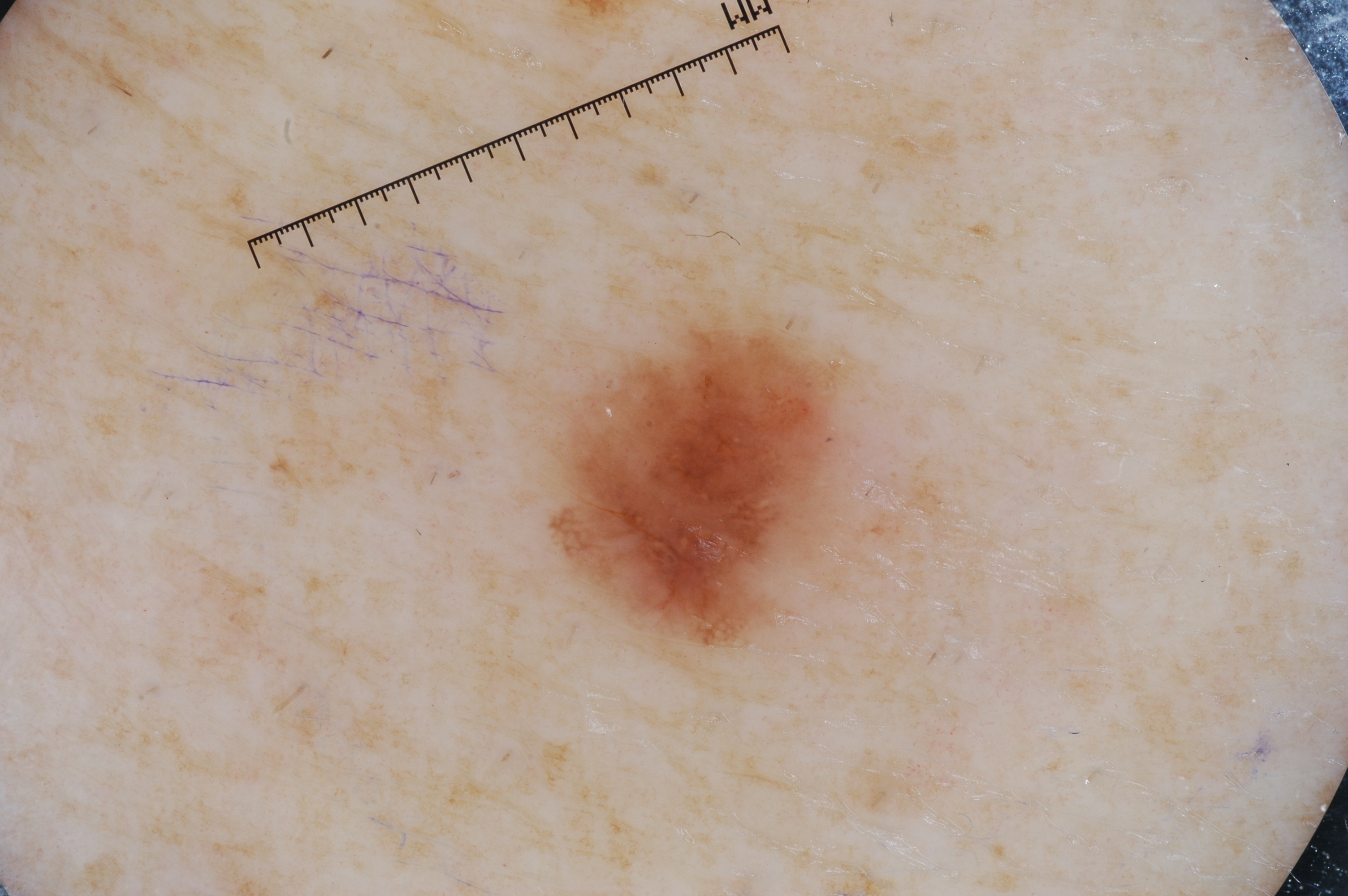Summary: A male subject, in their 60s. A dermoscopic image of a skin lesion. The lesion takes up about 7% of the image. Dermoscopy demonstrates negative network and pigment network, with no milia-like cysts or streaks. The visible lesion spans [548, 308, 853, 658]. Conclusion: Biopsy-confirmed as a melanoma, a skin cancer.